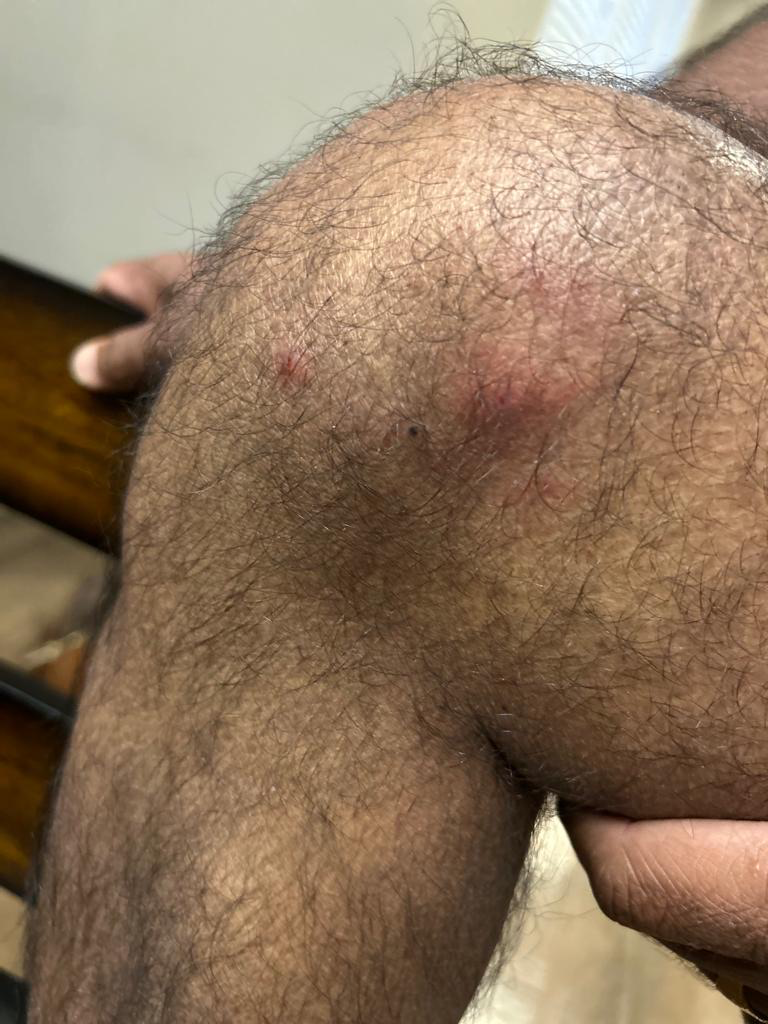No differential diagnosis could be assigned on photographic review. Reported lesion symptoms include darkening and itching. The lesion involves the leg. The photograph is a close-up of the affected area. The patient notes the lesion is raised or bumpy and fluid-filled.